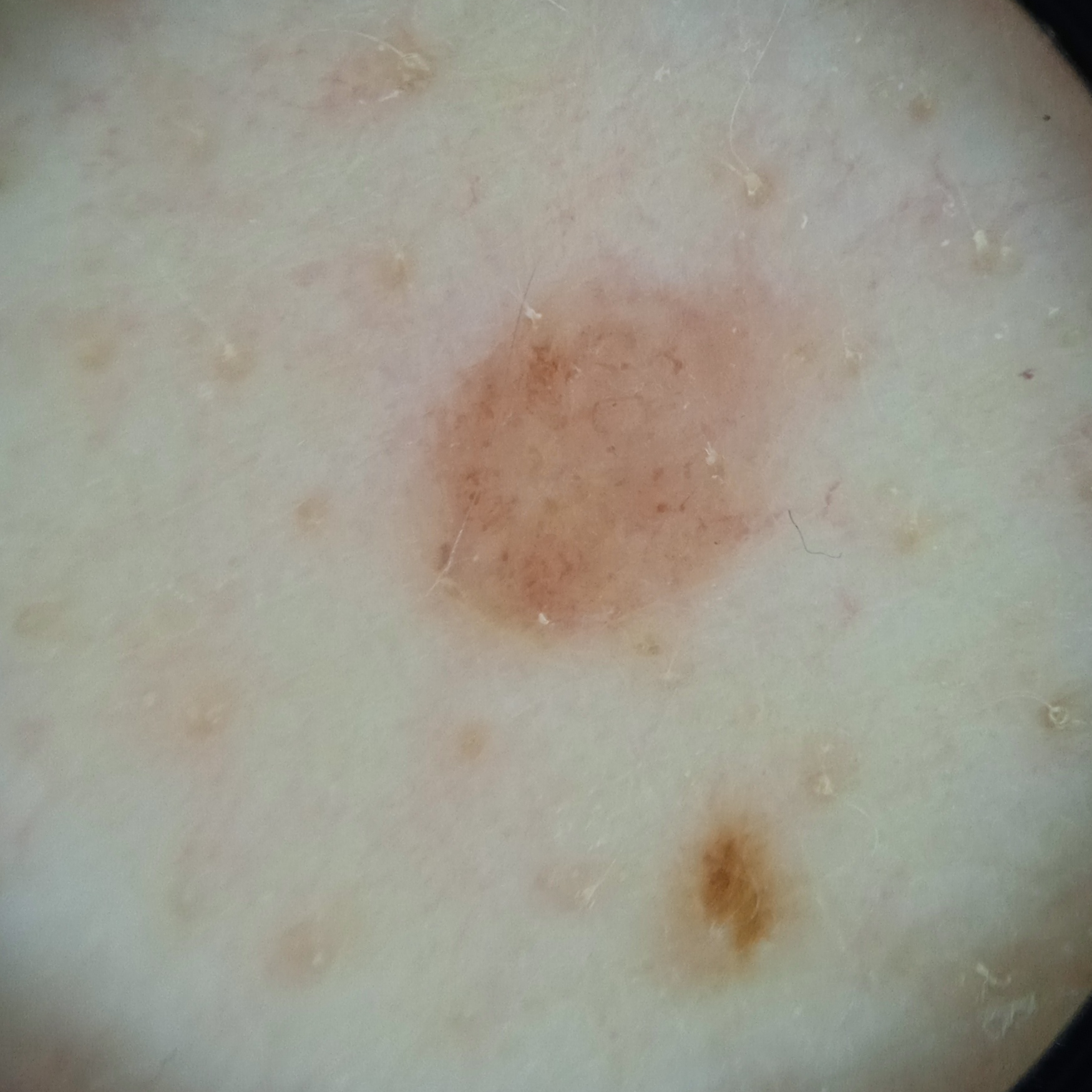A male subject age 65.
The patient says their skin reddens painfully with sun exposure.
Numerous moles by the patient's own estimate.
Acquired for a research image collection, with no referral diagnosis.
A dermoscopic image of a skin lesion.
The lesion is located on the back.
Measuring roughly 4.4 mm.
Four dermatologists reviewed the lesion; the consensus was a melanocytic nevus.